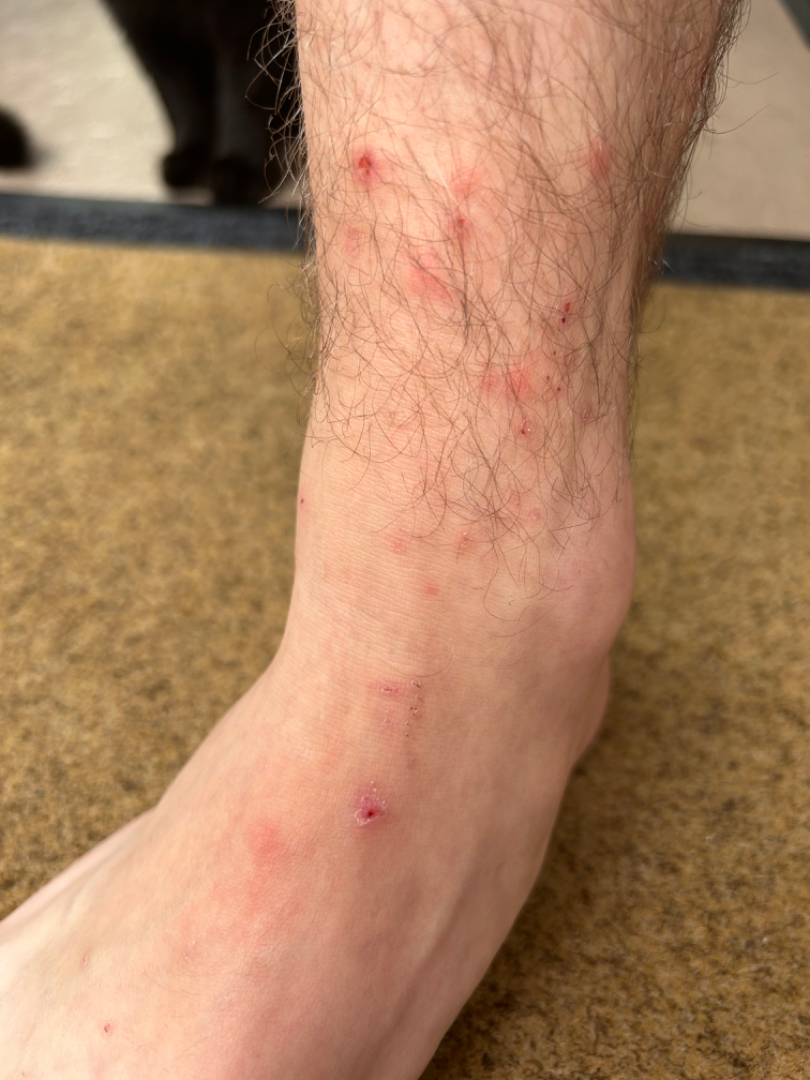| key | value |
|---|---|
| differential diagnosis | the impression was split between Insect Bite and Acute dermatitis, NOS |